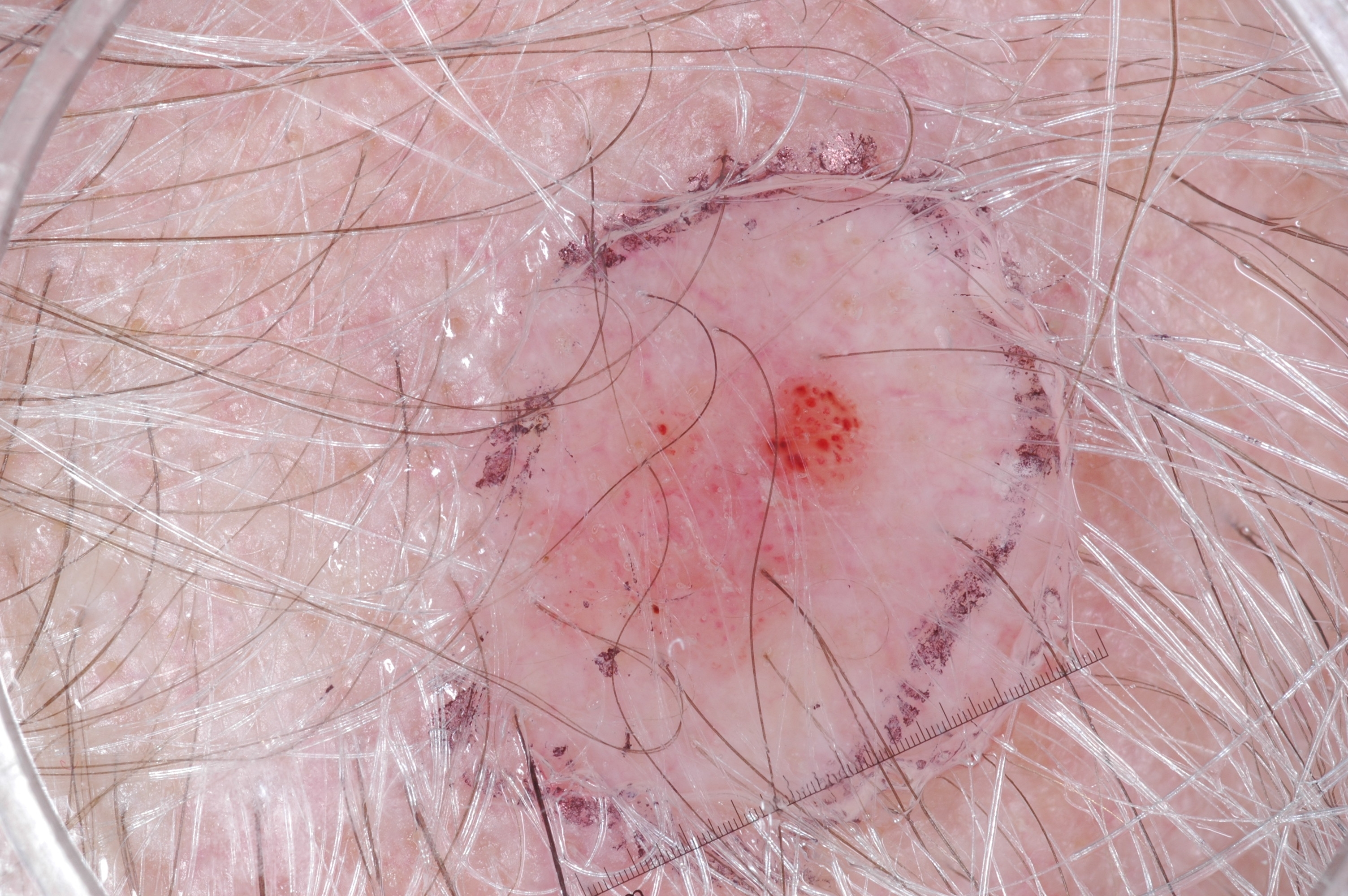Case summary: The subject is a male roughly 65 years of age. A dermoscopy image of a single skin lesion. The lesion spans x1=502 y1=322 x2=895 y2=705. Dermoscopic examination shows no negative network, streaks, milia-like cysts, or pigment network. A mid-sized lesion within the field. Impression: Clinically diagnosed as a seborrheic keratosis, a benign lesion.